The condition has been present for one to four weeks; the arm is involved; the photo was captured at a distance; self-categorized by the patient as a rash; texture is reported as raised or bumpy; the patient indicates itching: 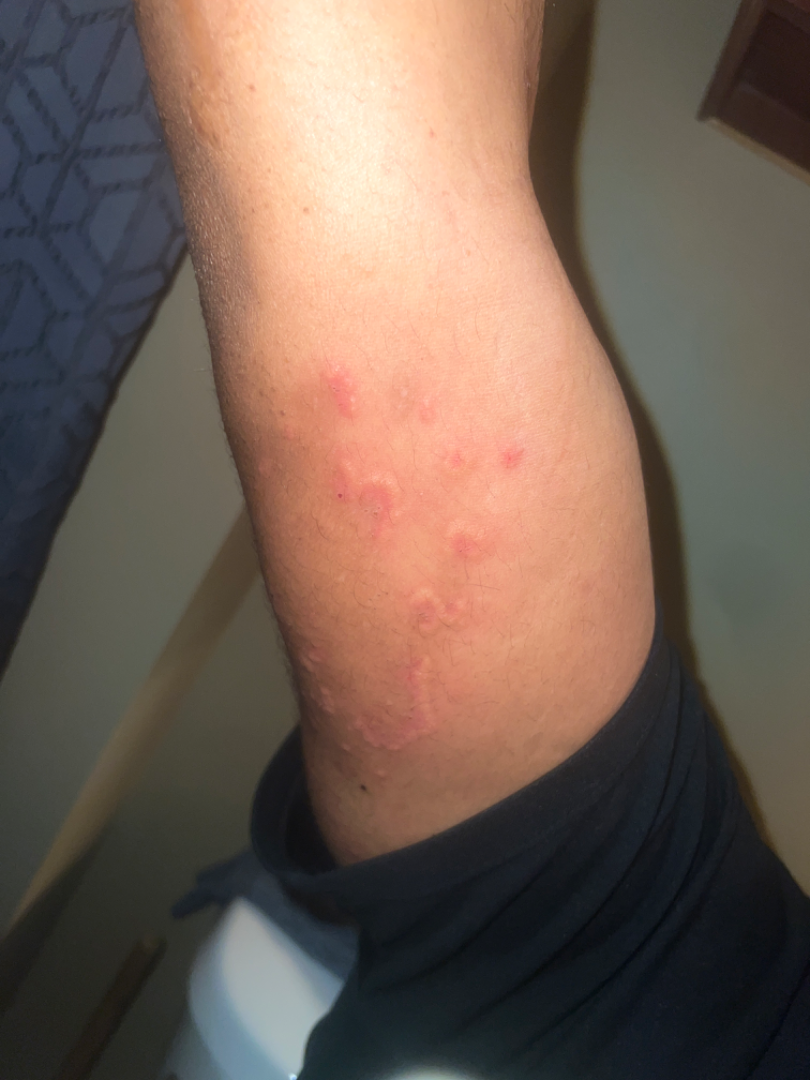{"differential": {"leading": ["Leukocytoclastic Vasculitis"], "considered": ["Erythema annulare centrifugum"]}}